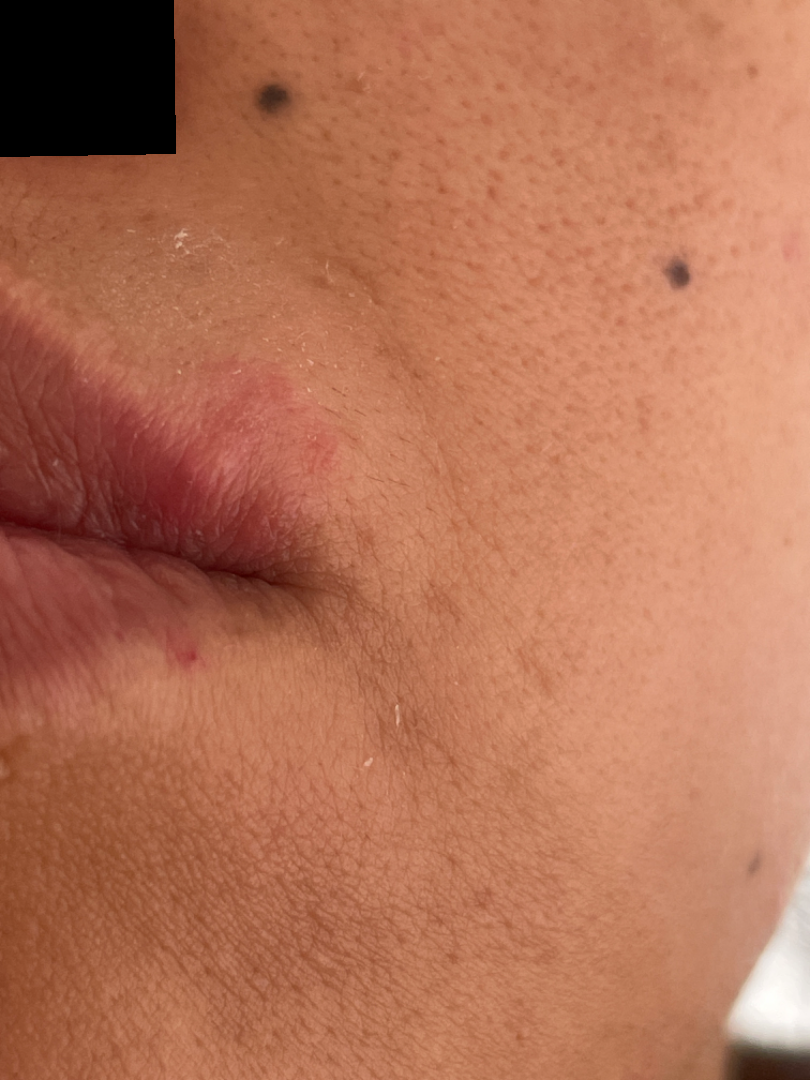<report>
<shot_type>close-up</shot_type>
<patient>female, age 30–39</patient>
<symptoms>itching</symptoms>
<differential>
  <leading>Herpes Simplex</leading>
  <considered>Allergic Contact Dermatitis</considered>
</differential>
</report>